A dermoscopic photograph of a skin lesion.
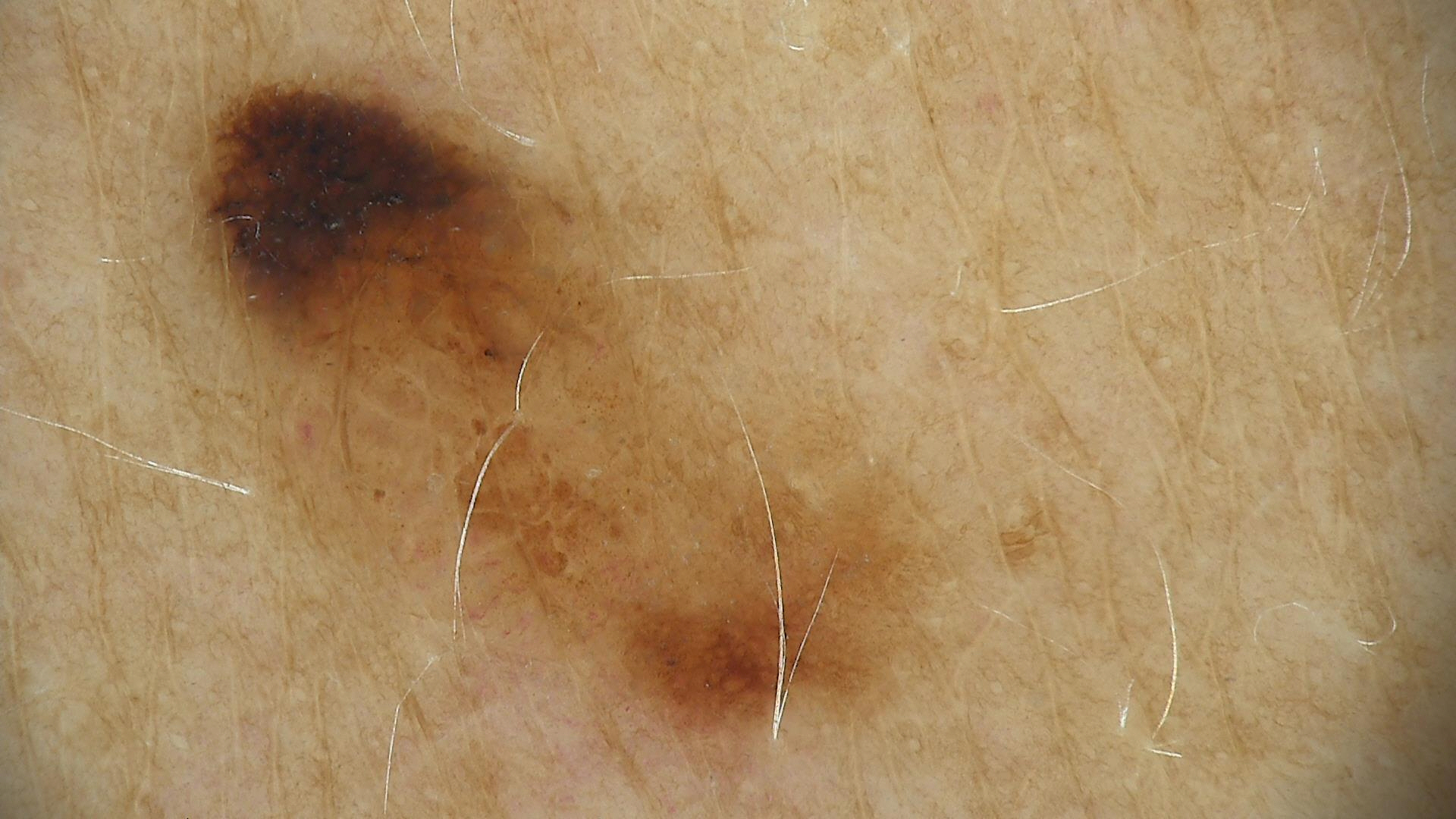{"diagnosis": {"name": "dysplastic junctional nevus", "code": "jd", "malignancy": "benign", "super_class": "melanocytic", "confirmation": "expert consensus"}}